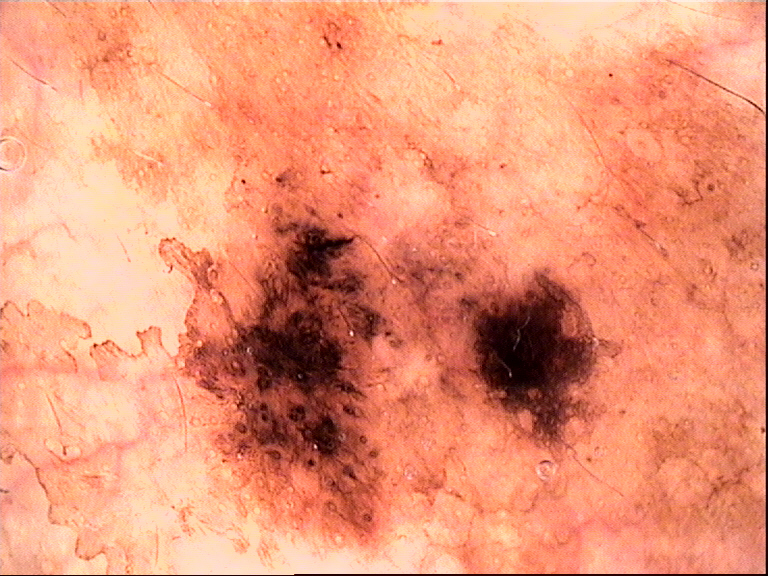Dermoscopy of a skin lesion. Histopathologically confirmed as a melanoma.